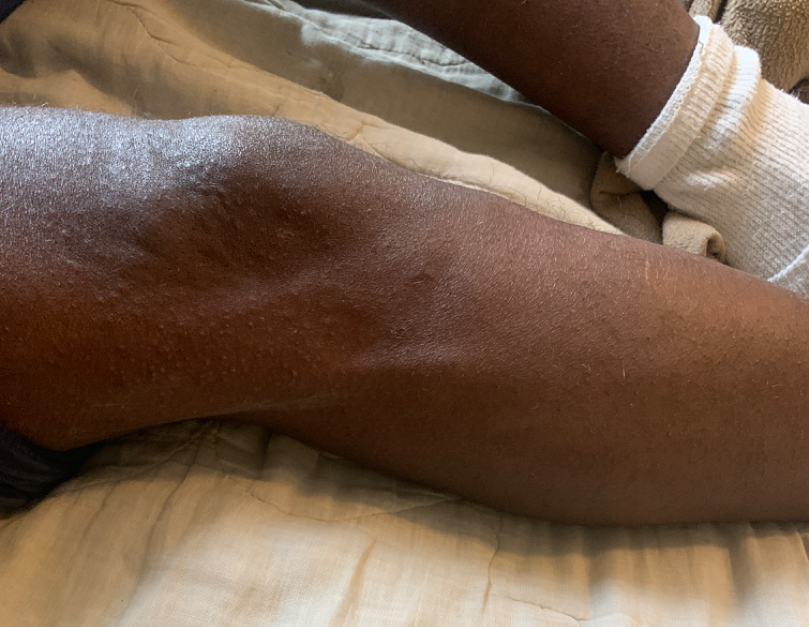The photo was captured at a distance. Texture is reported as fluid-filled and raised or bumpy. The patient considered this a rash. The lesion is associated with itching, bothersome appearance and burning. The contributor is a male aged 18–29. The back of the hand, leg and arm are involved. The patient reports the condition has been present for less than one week. On remote dermatologist review, in keeping with Eczema.